A male subject aged around 70, a dermoscopy image of a single skin lesion.
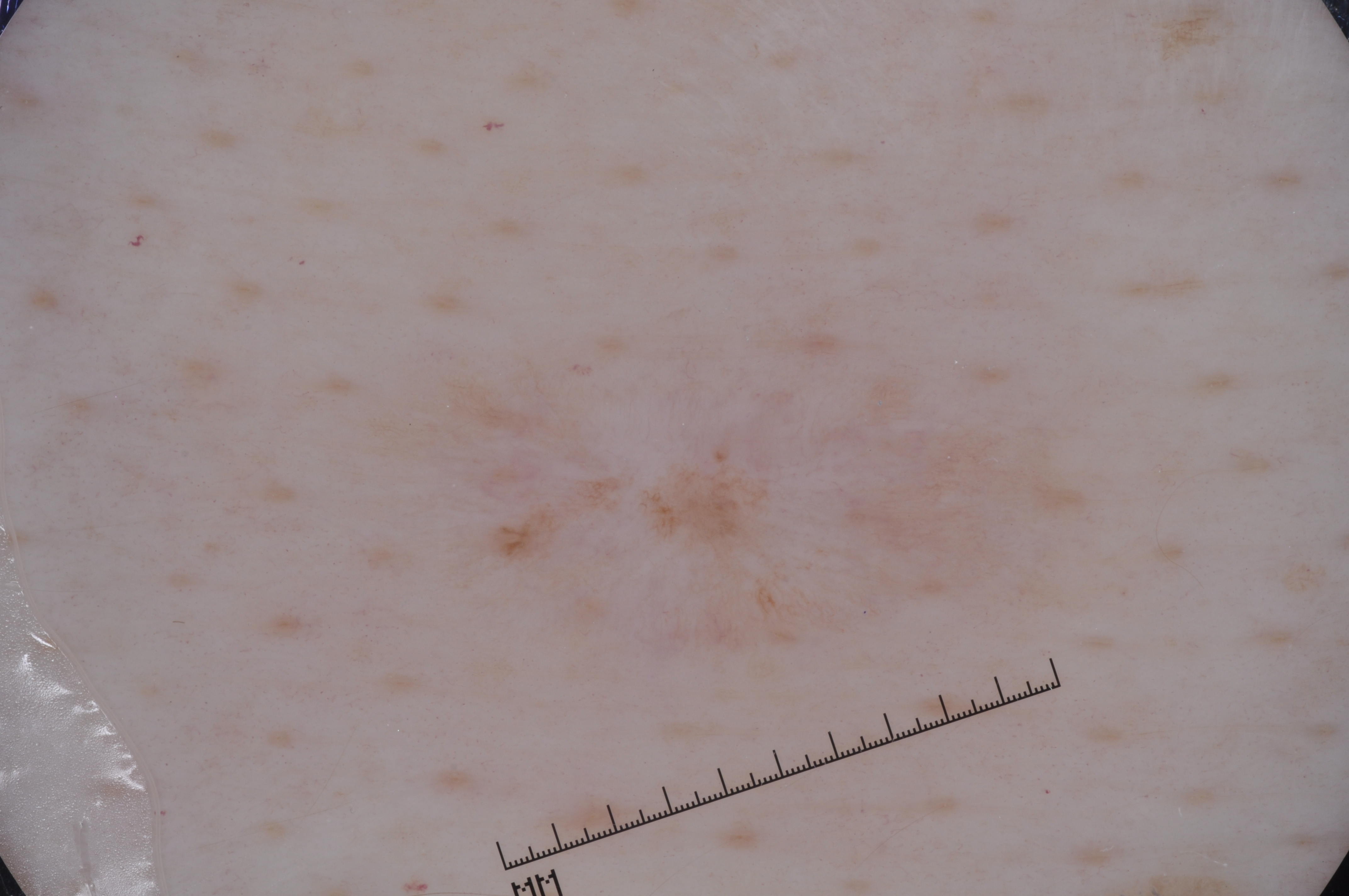features=pigment network; absent: negative network, milia-like cysts, and streaks | lesion bbox=box(466, 323, 1004, 658) | diagnosis=a melanocytic nevus, a benign skin lesion.